A smartphone photograph of a skin lesion. A male subject in their mid-60s.
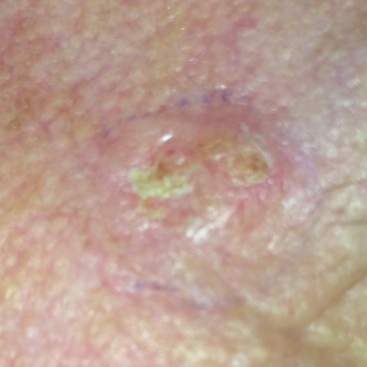<skin_lesion>
  <symptoms>
    <present>elevation, itching</present>
  </symptoms>
  <diagnosis>
    <name>basal cell carcinoma</name>
    <code>BCC</code>
    <malignancy>malignant</malignancy>
    <confirmation>histopathology</confirmation>
  </diagnosis>
</skin_lesion>